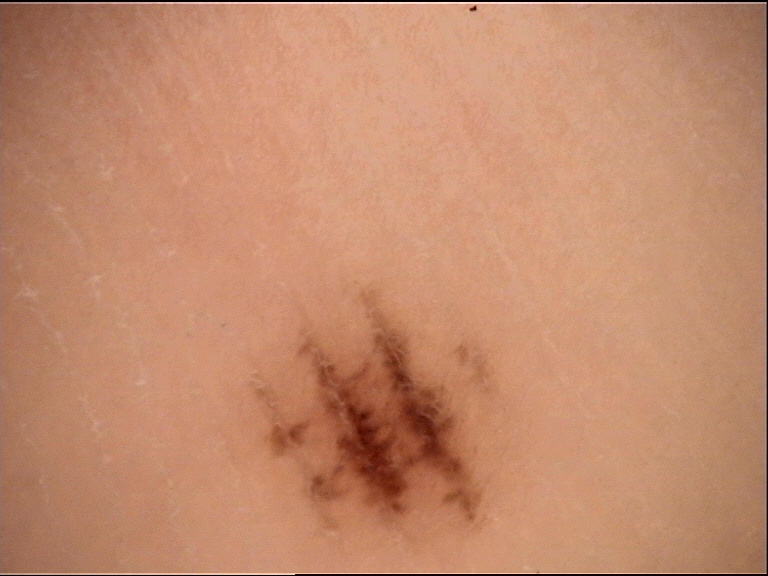Classified as a banal lesion — an acral junctional nevus.